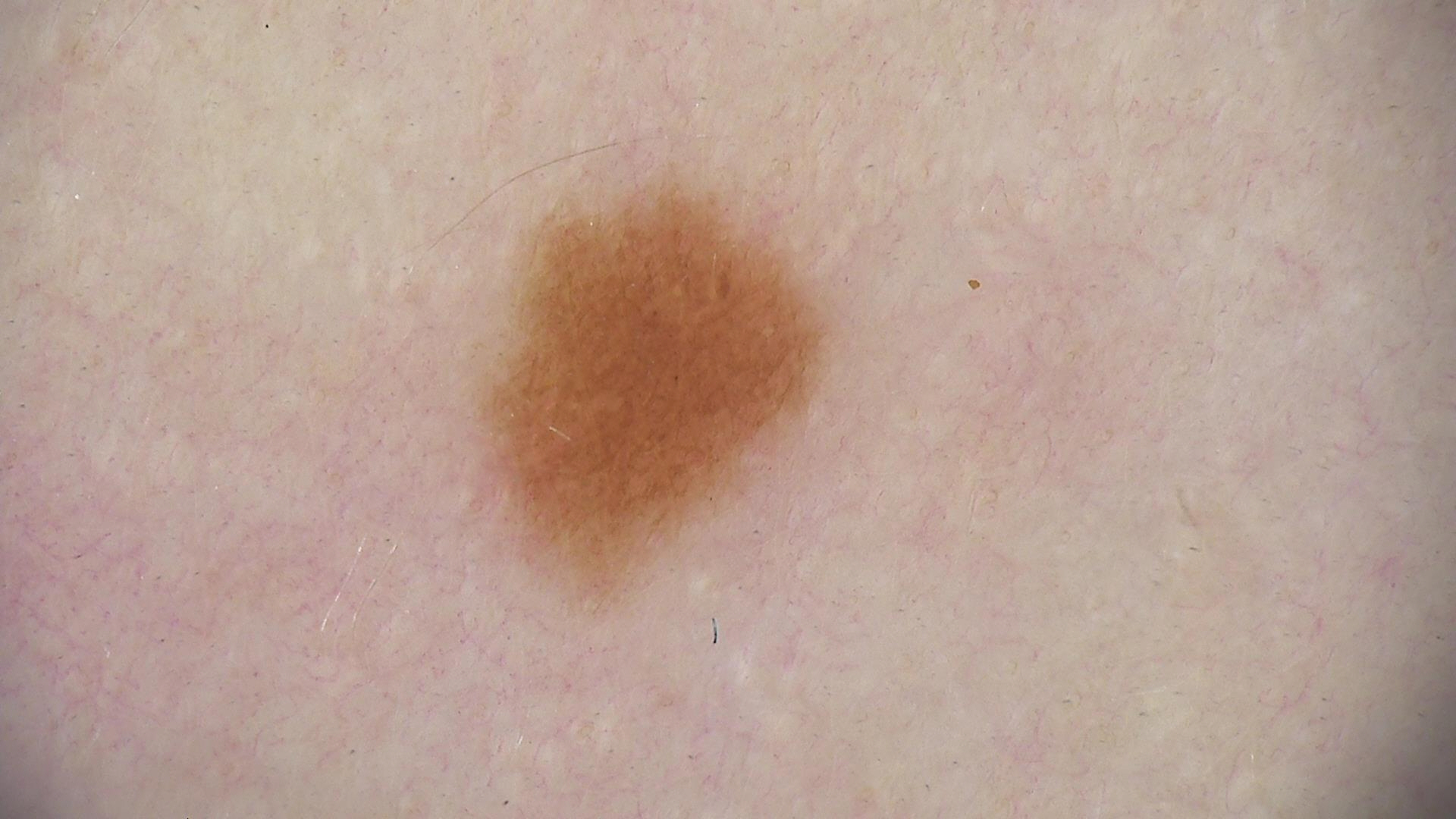modality: dermoscopy
diagnostic label: dysplastic junctional nevus (expert consensus)